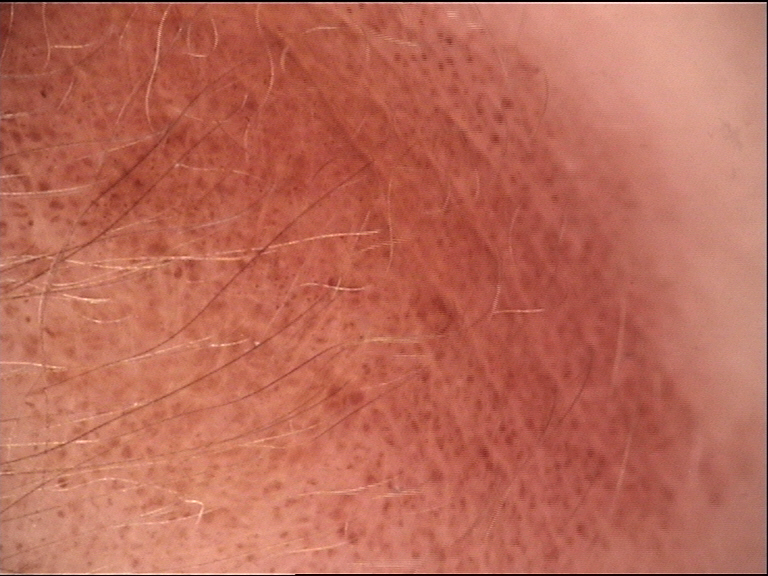Impression:
The diagnostic label was a congenital junctional nevus.